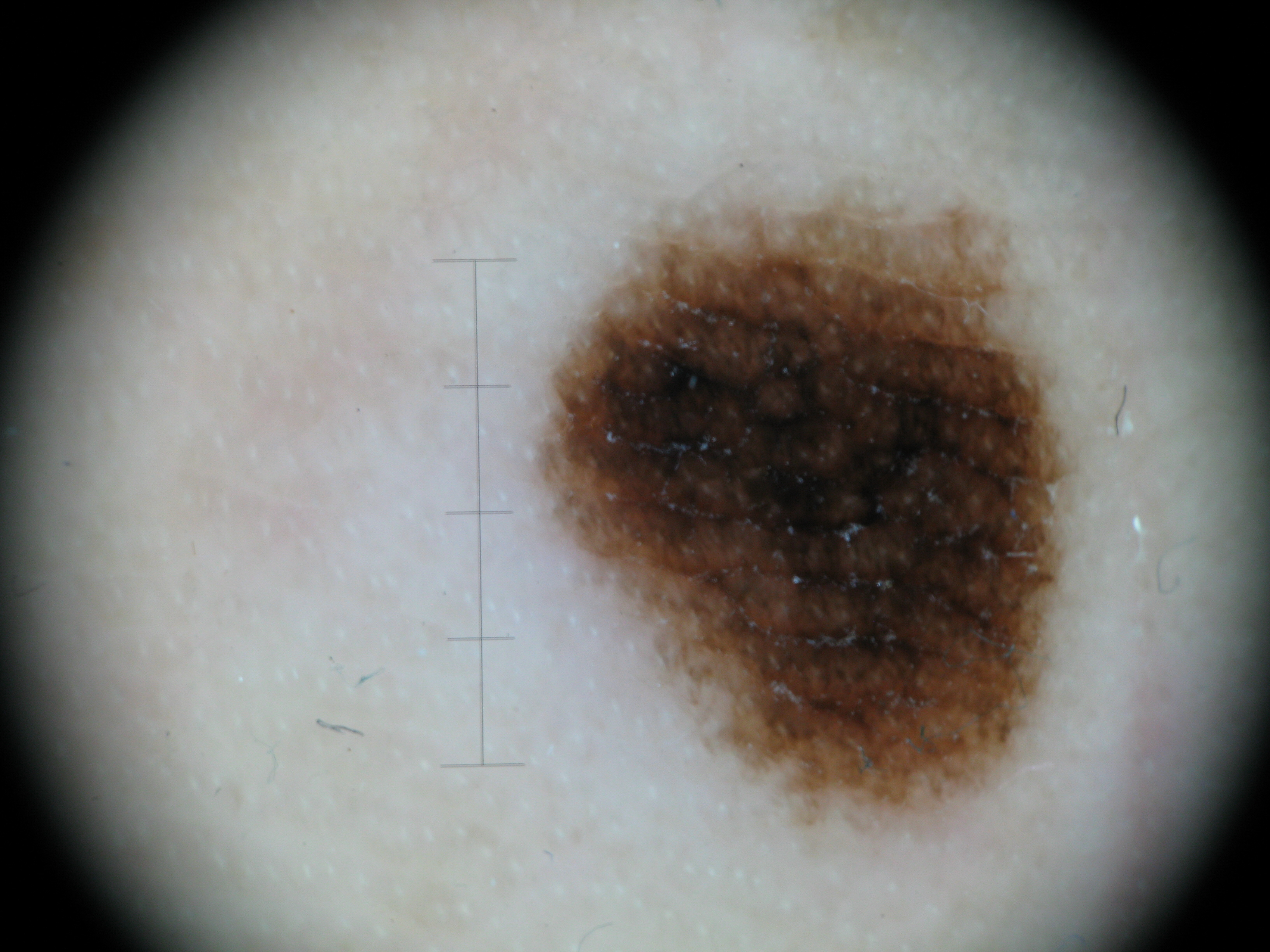Diagnosed as an acral junctional nevus.